A clinical photo of a skin lesion taken with a smartphone · Fitzpatrick phototype II · the chart records prior malignancy (patient or family) — 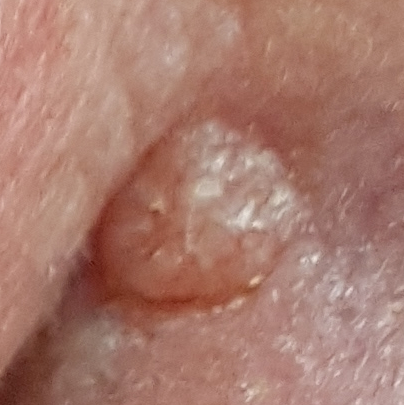Q: Where on the body is the lesion?
A: the nose
Q: Lesion size?
A: 5 × 5 mm
Q: What is the diagnosis?
A: basal cell carcinoma (biopsy-proven)